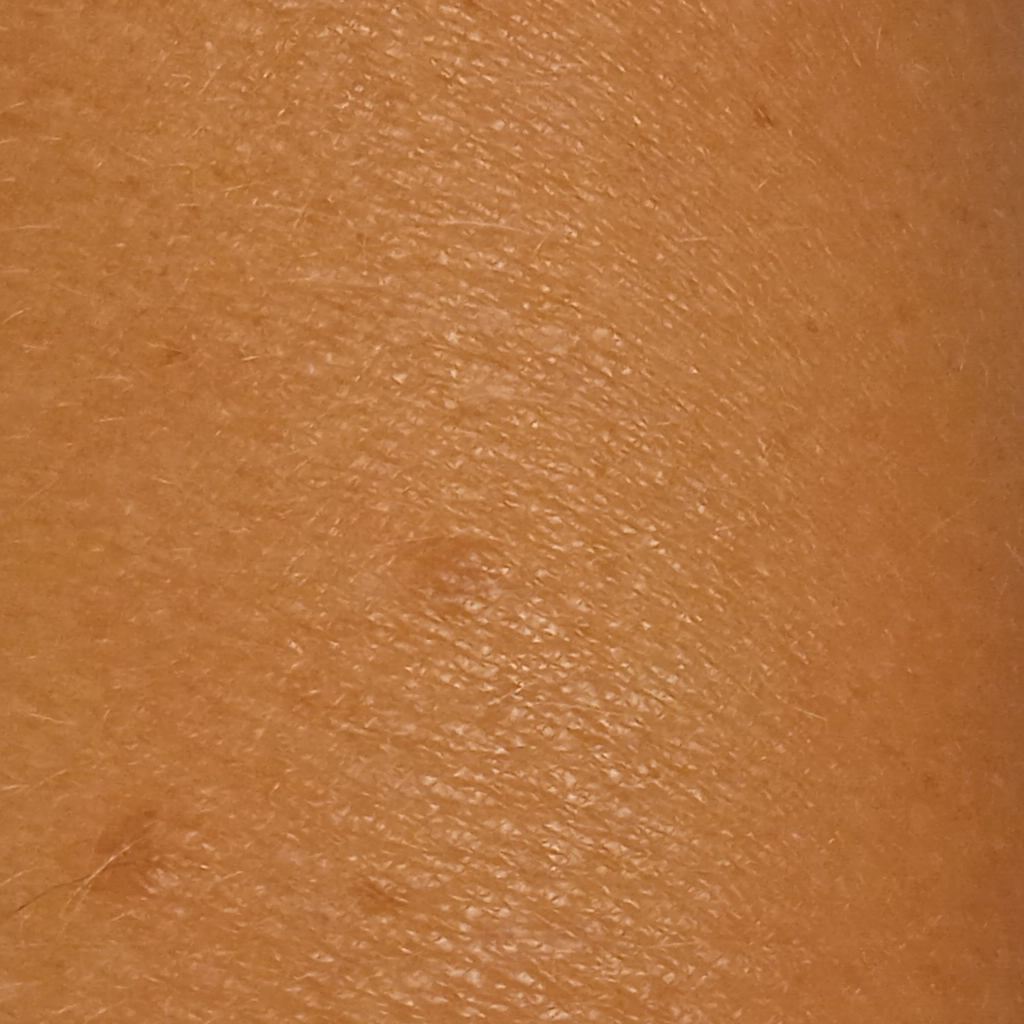A confident diagnosis could not be established from review. Summary:
The patient says their skin tans without first burning. The patient reports a history of sunbed use. Imaged for a research study, with no referral diagnosis recorded. A clinical photograph showing a skin lesion. A moderate number of moles by the patient's own estimate. The lesion is on the back. The lesion measures approximately 3.5 mm.